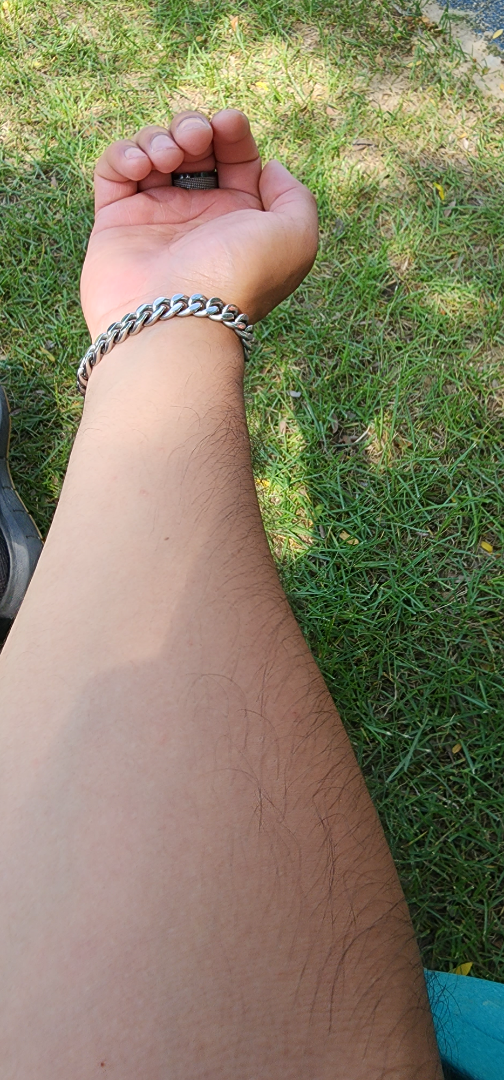The contributor reports itching. This image was taken at a distance. The contributor reports the condition has been present for less than one week. The patient described the issue as acne. The lesion involves the arm. The contributor reports the lesion is raised or bumpy. Male patient, age 30–39. On remote review of the image: the differential includes Insect Bite and Folliculitis, with no clear leading consideration.